The photograph was taken at an angle — 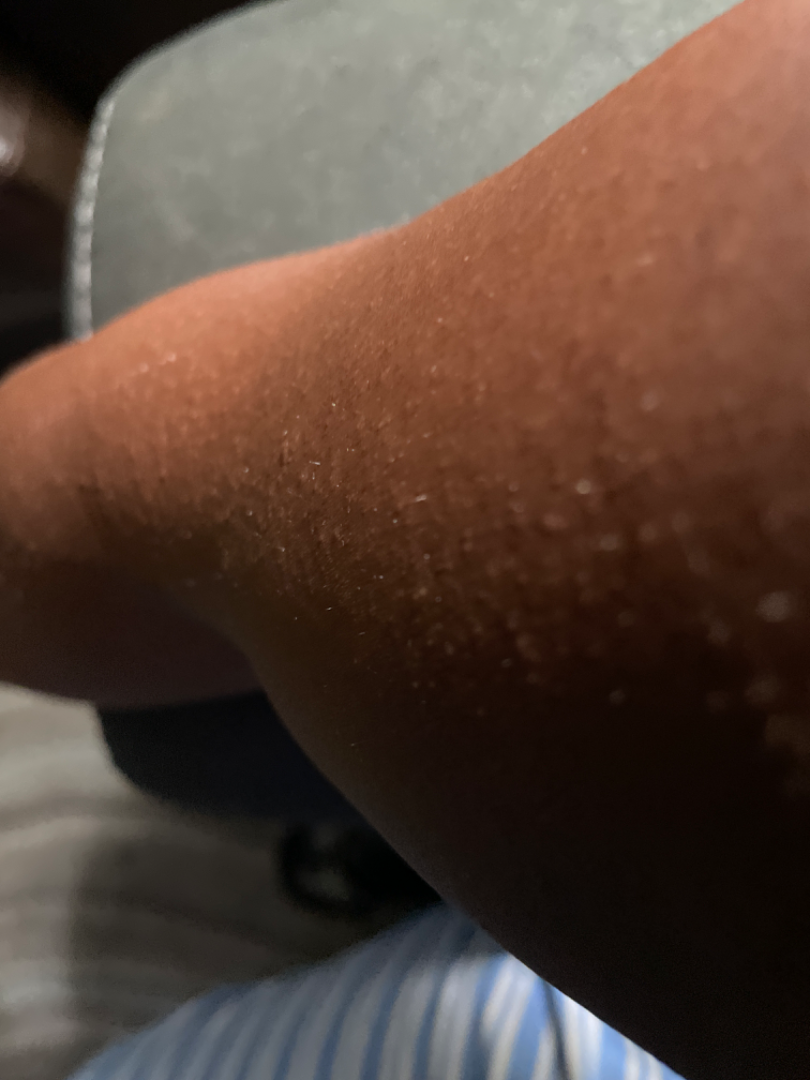assessment=could not be assessed.